The photograph was taken at an angle. The lesion involves the top or side of the foot. The patient is a male aged 40–49.
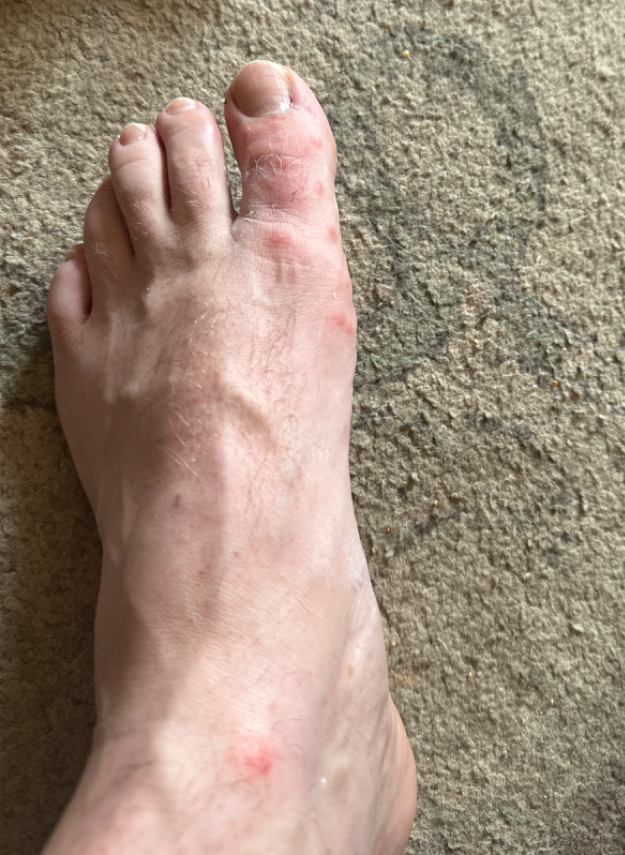assessment: consistent with Insect Bite